Symptoms reported: bothersome appearance, pain, burning, bleeding, itching and enlargement · no relevant systemic symptoms · the photograph was taken at a distance · the lesion is described as raised or bumpy, fluid-filled and rough or flaky · the lesion involves the arm, palm and back of the hand.
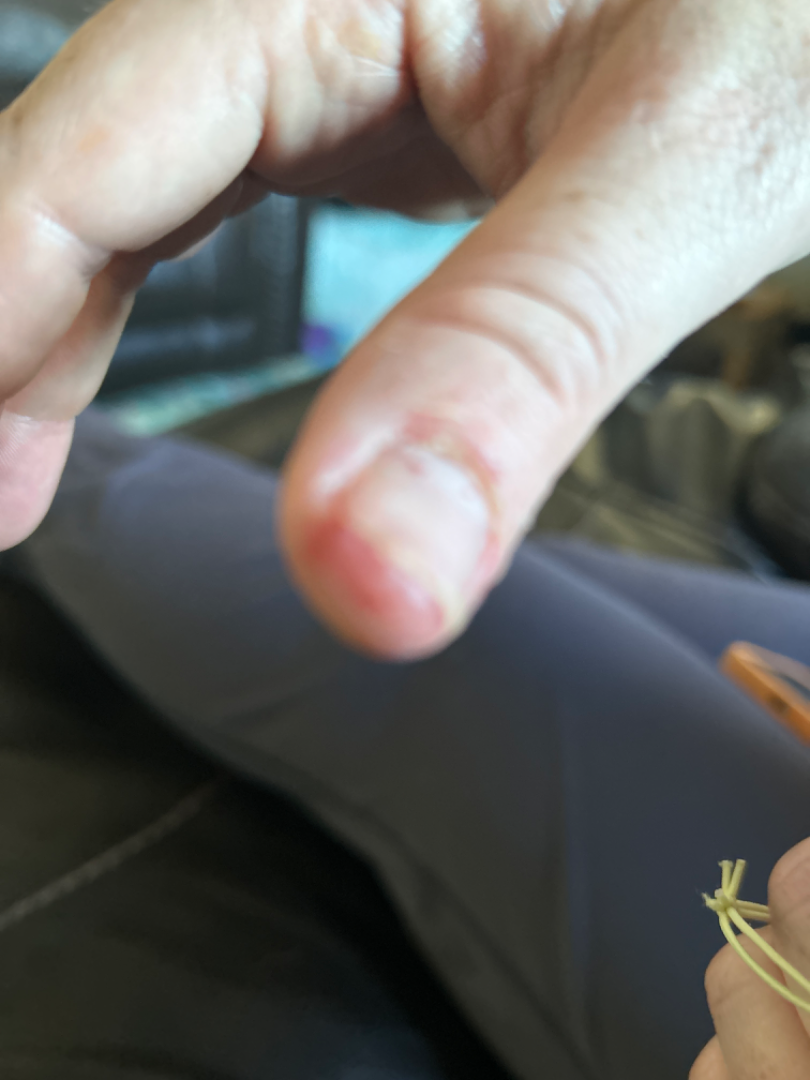The reviewing clinician's impression was: the favored diagnosis is Allergic Contact Dermatitis; also on the differential is Impetigo; also raised was Eczema.